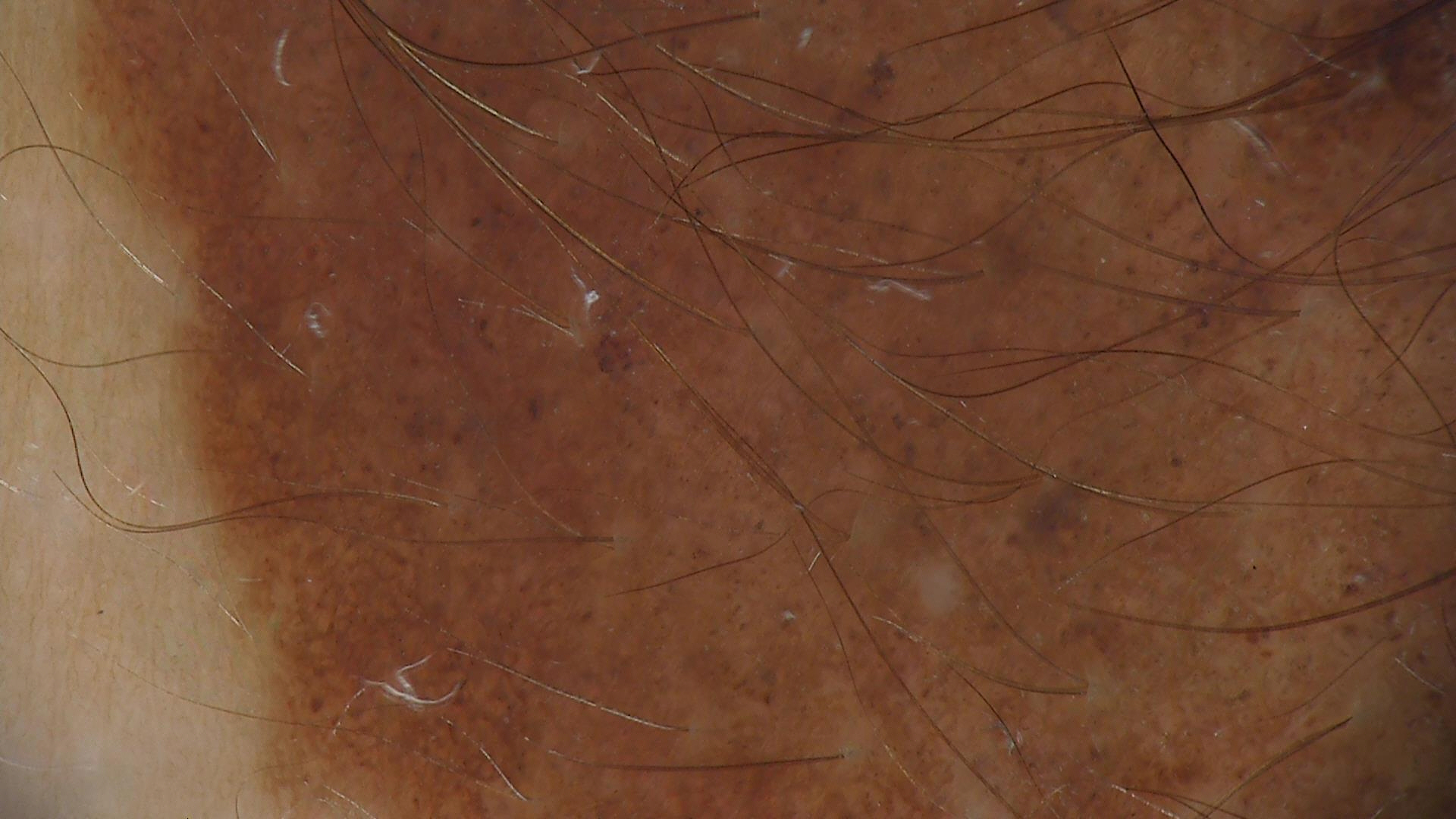imaging = dermoscopy
class = congenital junctional nevus (expert consensus)